A dermoscopic photograph of a skin lesion.
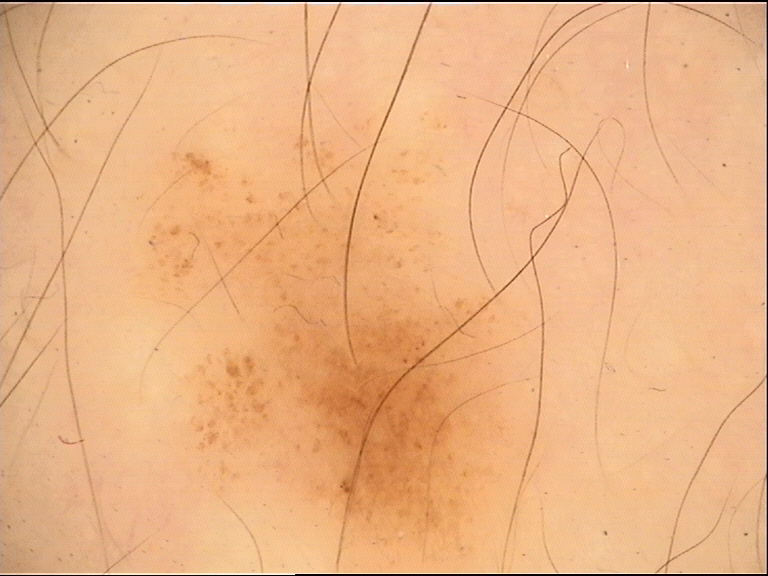Labeled as a dysplastic junctional nevus.